A dermoscopic close-up of a skin lesion: 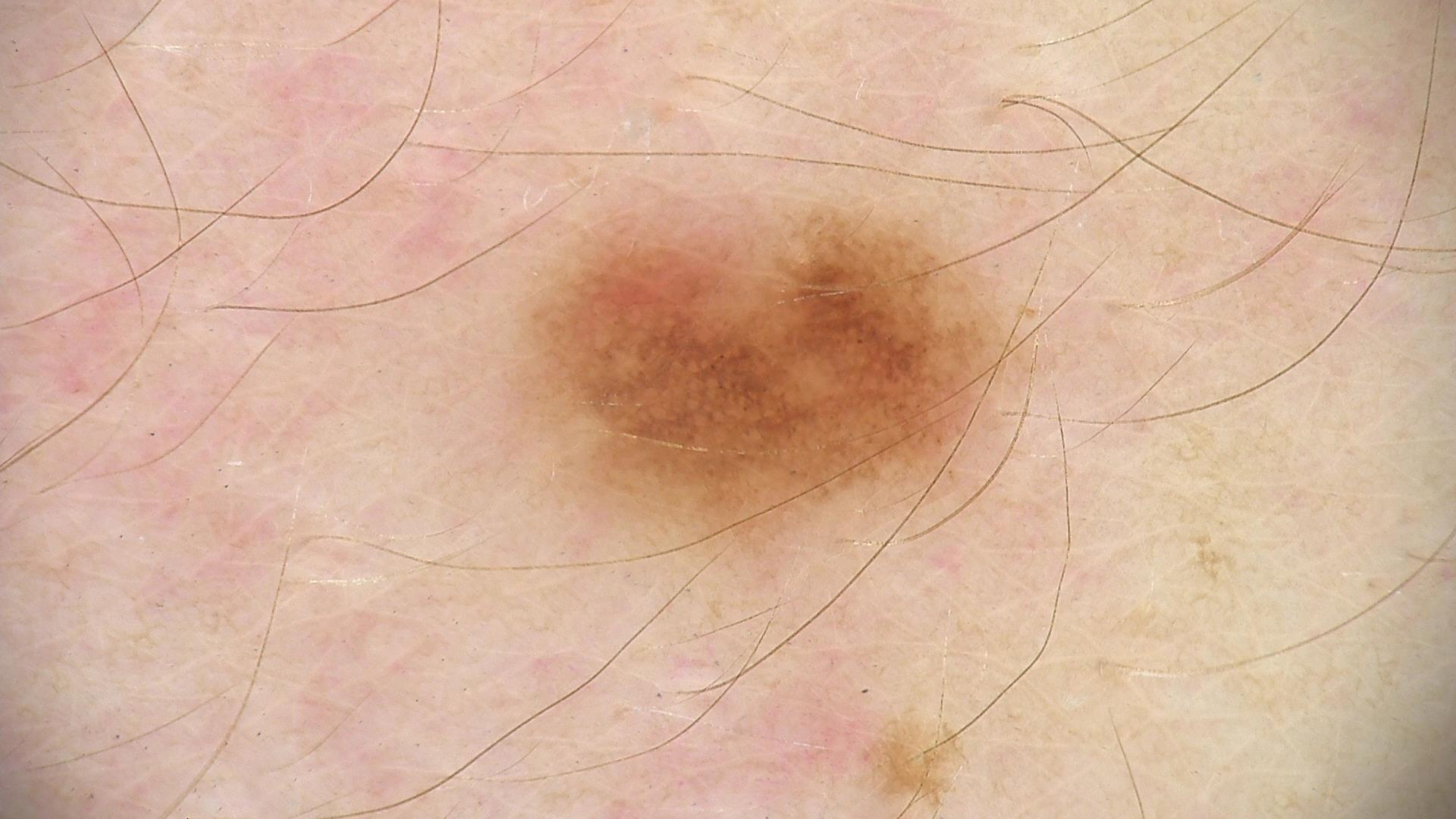The diagnostic label was a benign lesion — a dysplastic junctional nevus.